A female subject approximately 15 years of age · a skin lesion imaged with a dermatoscope:
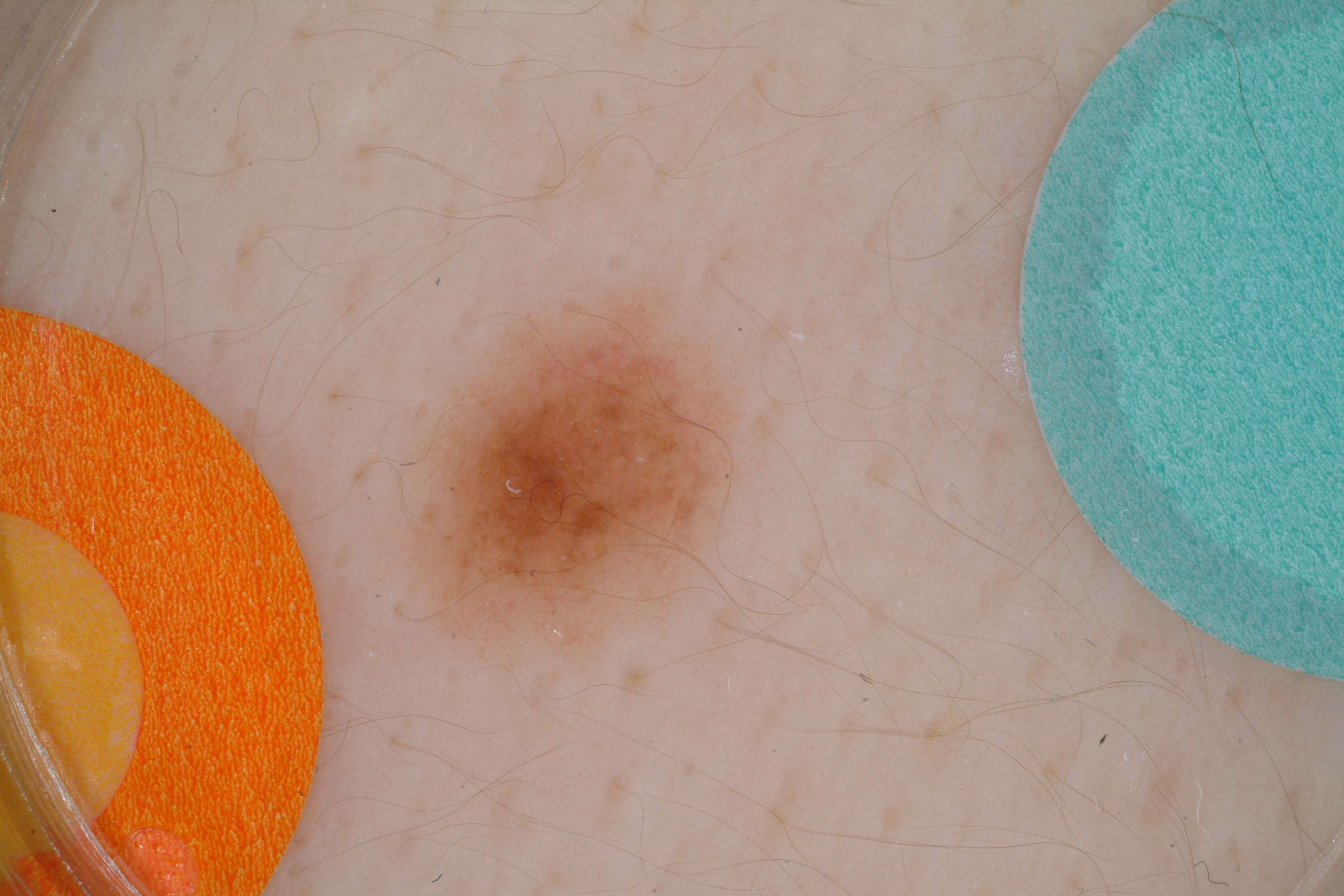{"lesion_location": {"bbox_xyxy": [367, 279, 747, 682]}, "lesion_extent": {"approx_field_fraction_pct": 9}, "dermoscopic_features": {"present": ["milia-like cysts"], "absent": ["streaks", "pigment network", "negative network", "globules"]}, "diagnosis": {"name": "melanocytic nevus", "malignancy": "benign", "lineage": "melanocytic", "provenance": "clinical"}}